A clinical close-up photograph of a skin lesion. A female subject age 16:
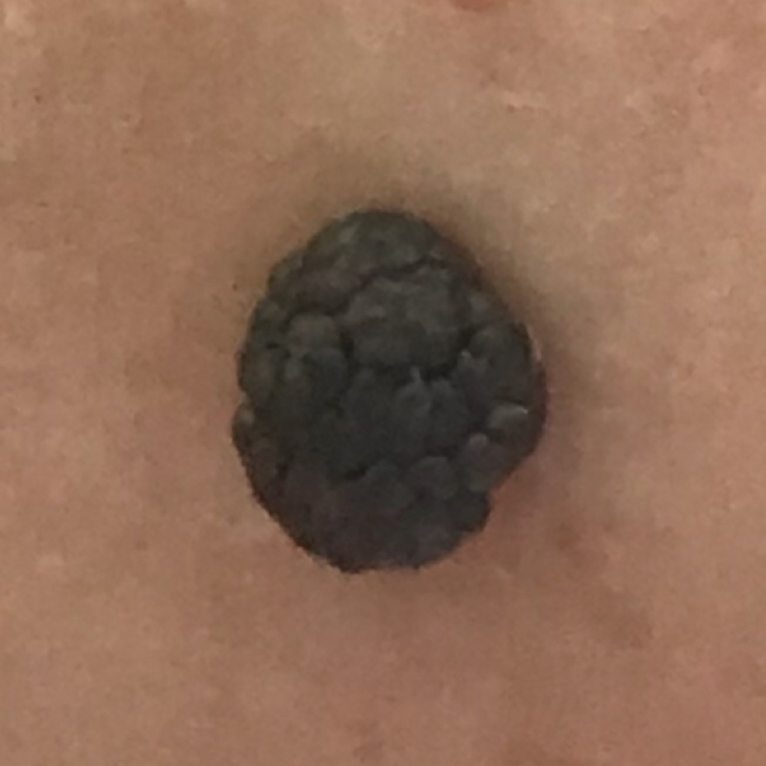The lesion involves the face. The lesion measures approximately 8 × 7 mm. Biopsy-confirmed as a benign skin lesion — a nevus.